A clinical photo of a skin lesion taken with a smartphone · a male patient aged 57 — 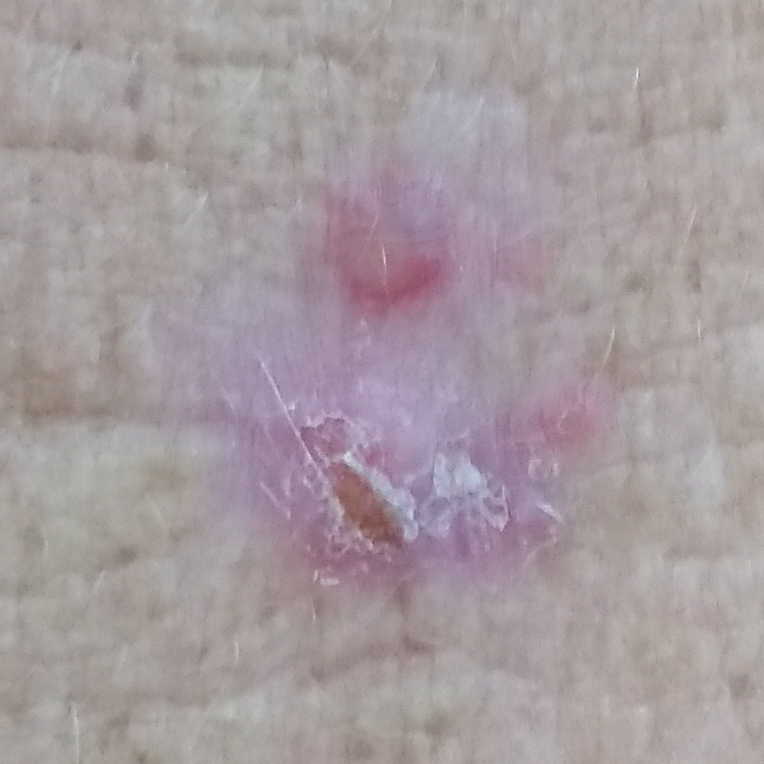Summary:
Located on a forearm. By the patient's account, the lesion has bled, is elevated, hurts, and itches.
Conclusion:
On biopsy, the diagnosis was a basal cell carcinoma.